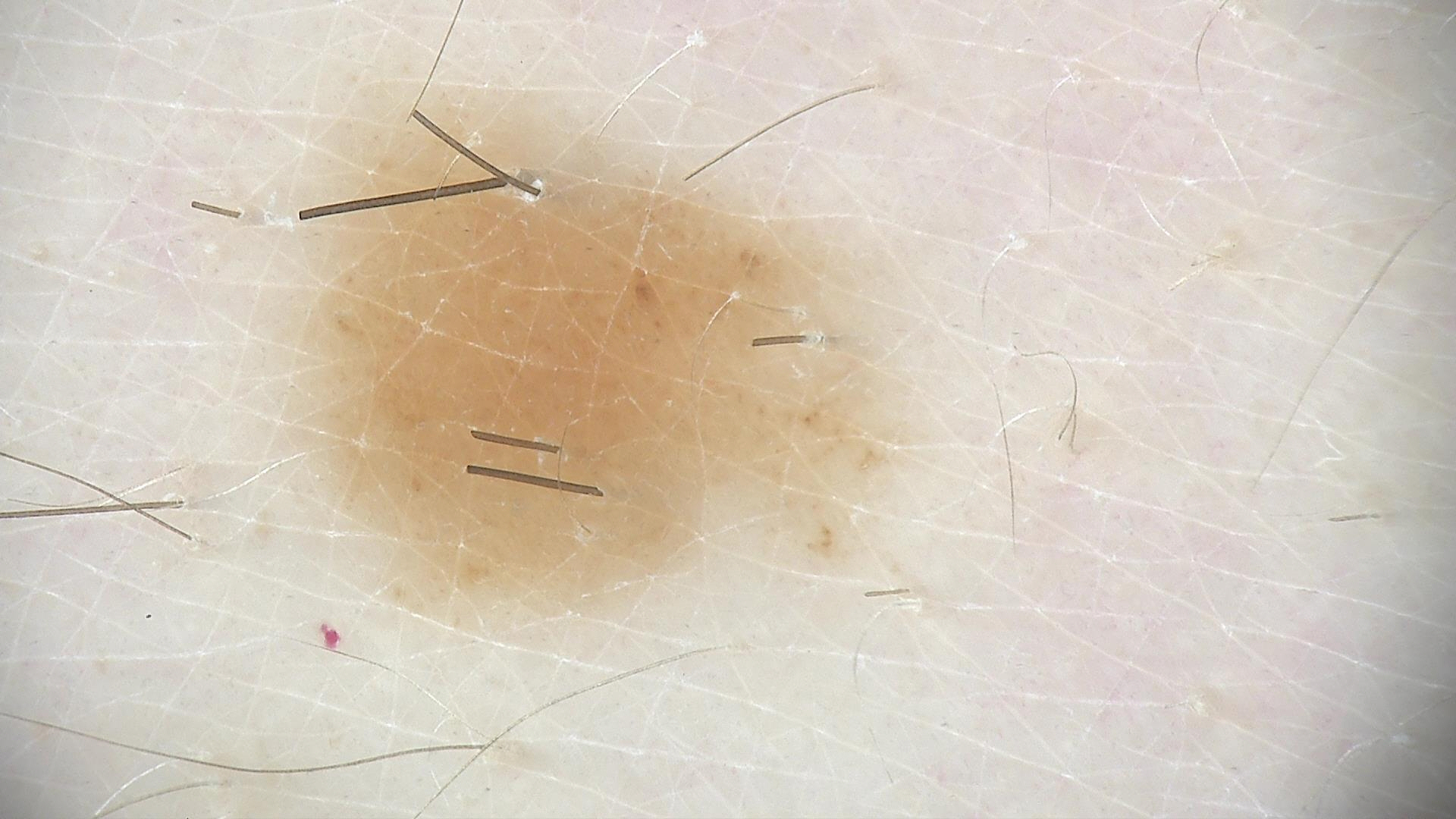Diagnosed as a benign lesion — a dysplastic junctional nevus.